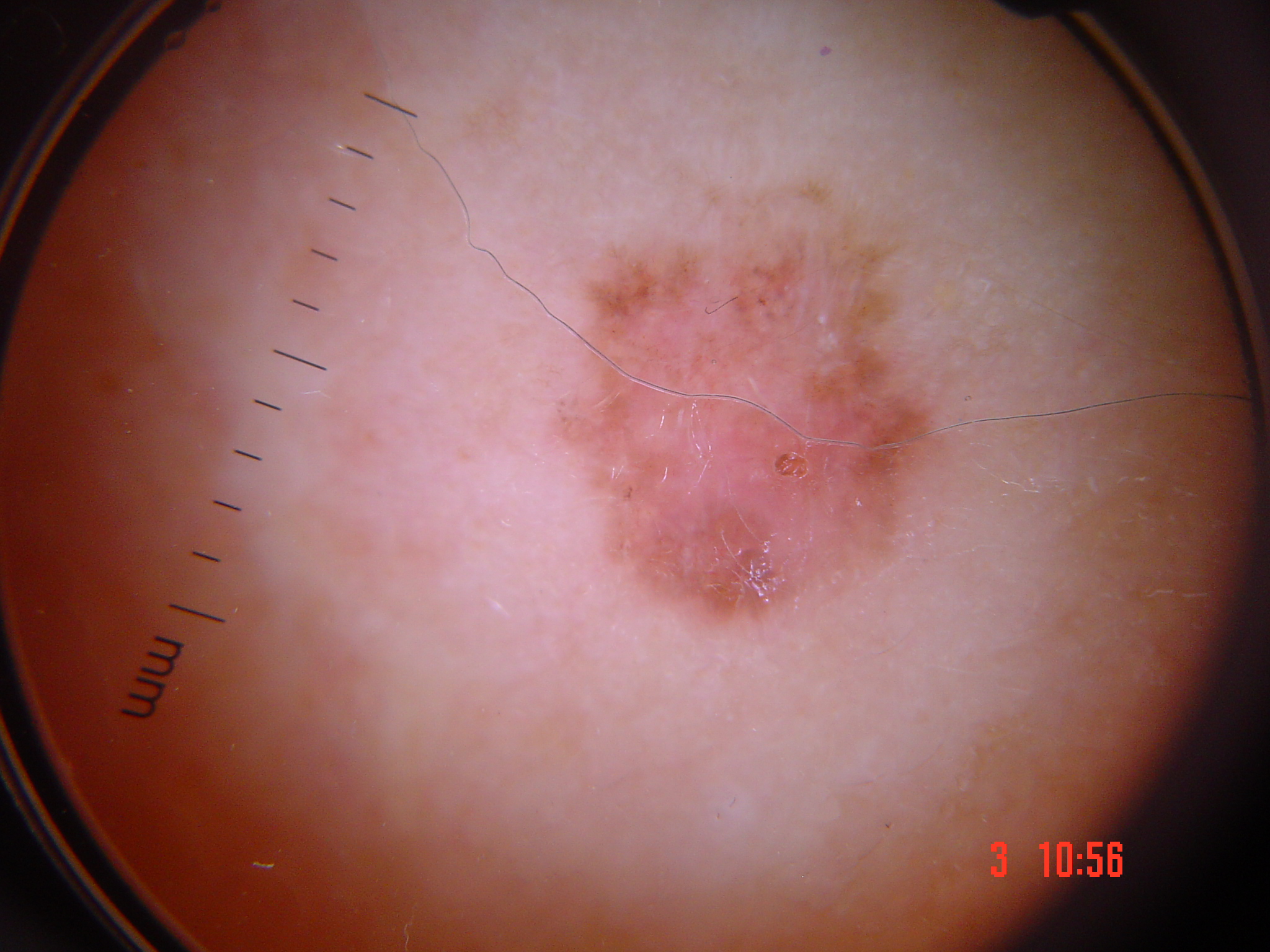{"diagnosis": {"name": "basal cell carcinoma", "code": "bcc", "malignancy": "malignant", "super_class": "non-melanocytic", "confirmation": "histopathology"}}